A dermatoscopic image of a skin lesion.
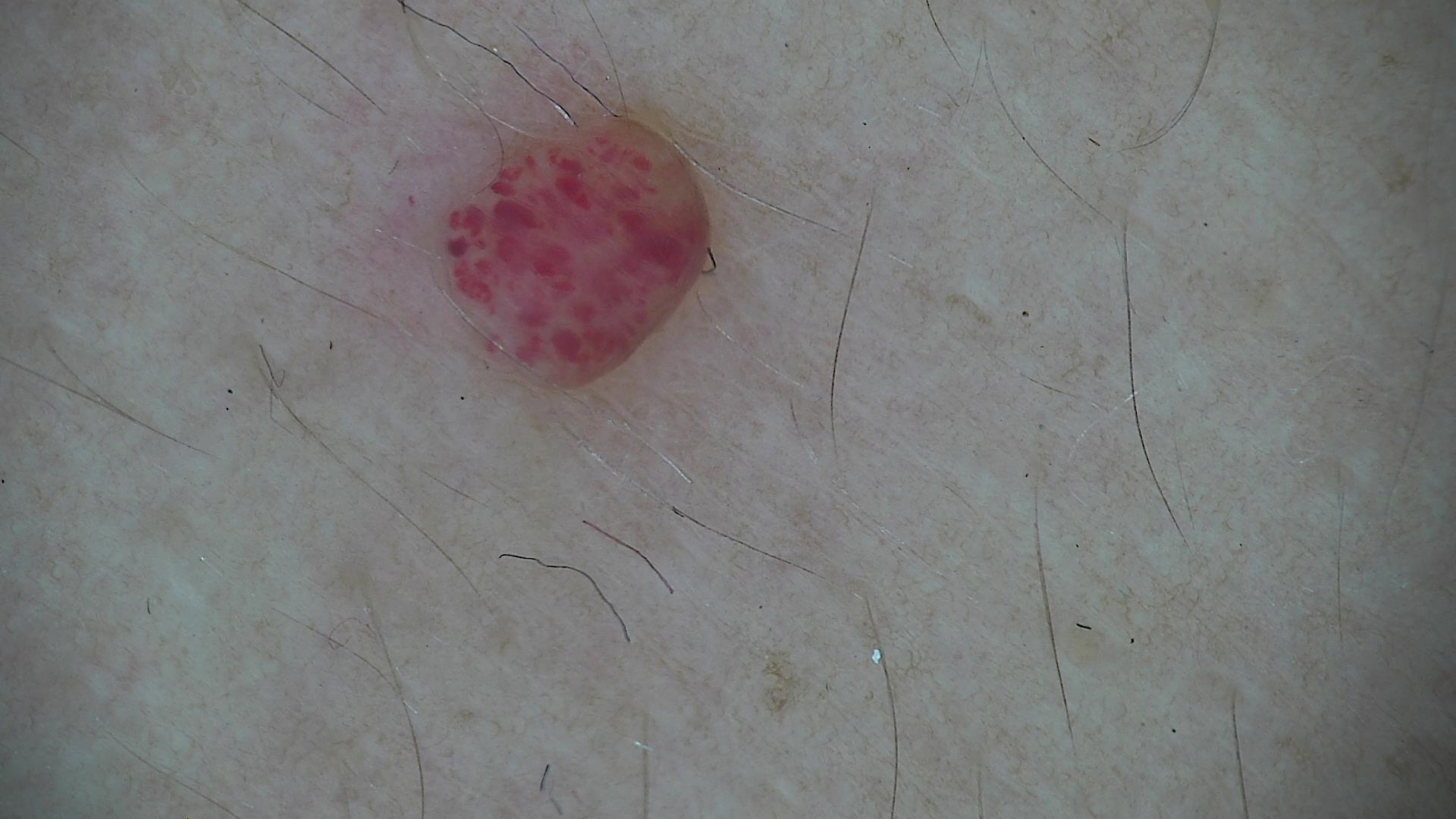Q: What kind of lesion is this?
A: vascular
Q: What is the diagnosis?
A: hemangioma (expert consensus)